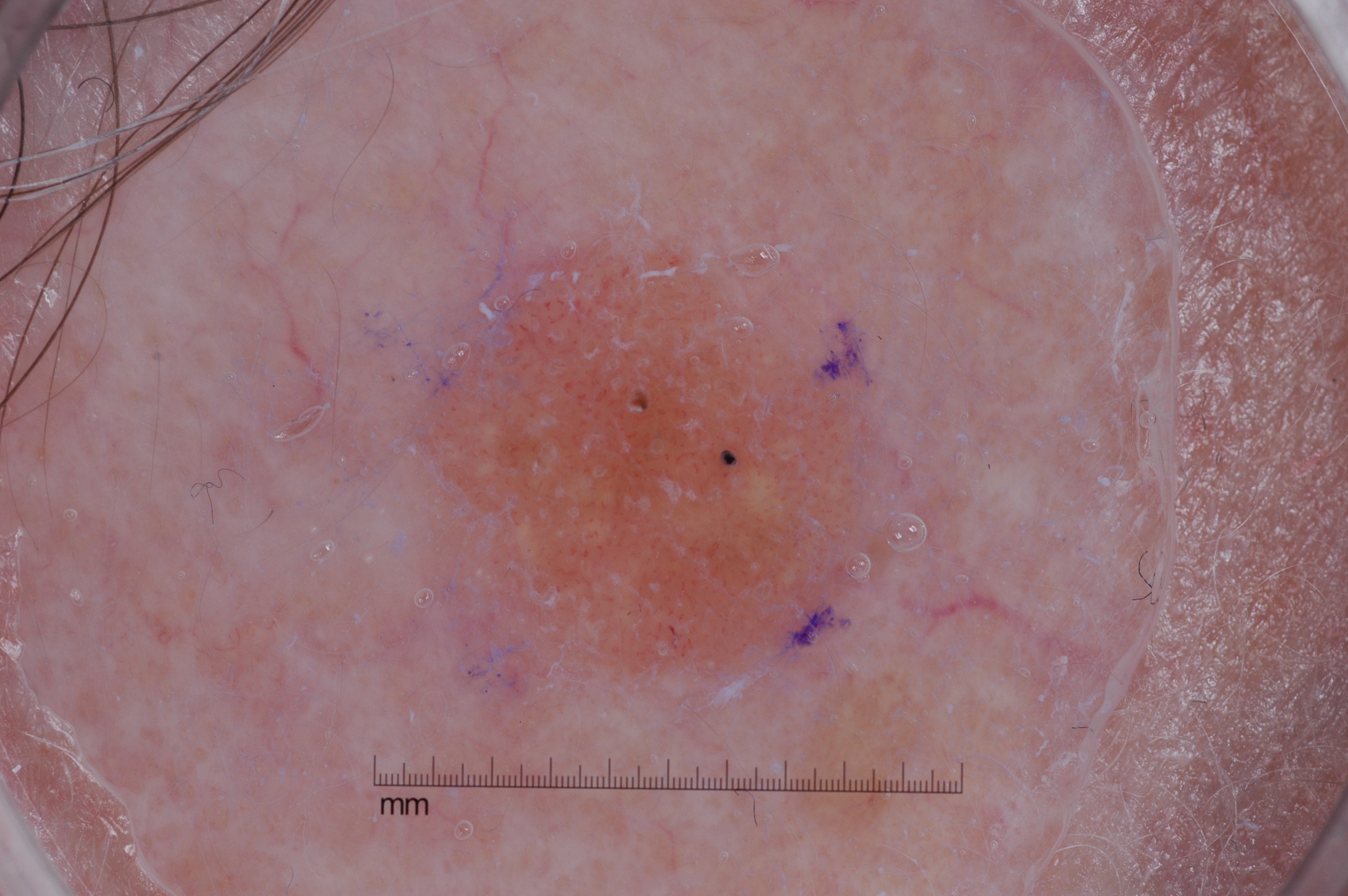| feature | finding |
|---|---|
| image | dermoscopic image |
| lesion size | ~11% of the field |
| lesion location | (422, 252, 863, 672) |
| features | milia-like cysts; absent: streaks, negative network, and pigment network |
| diagnostic label | a seborrheic keratosis |